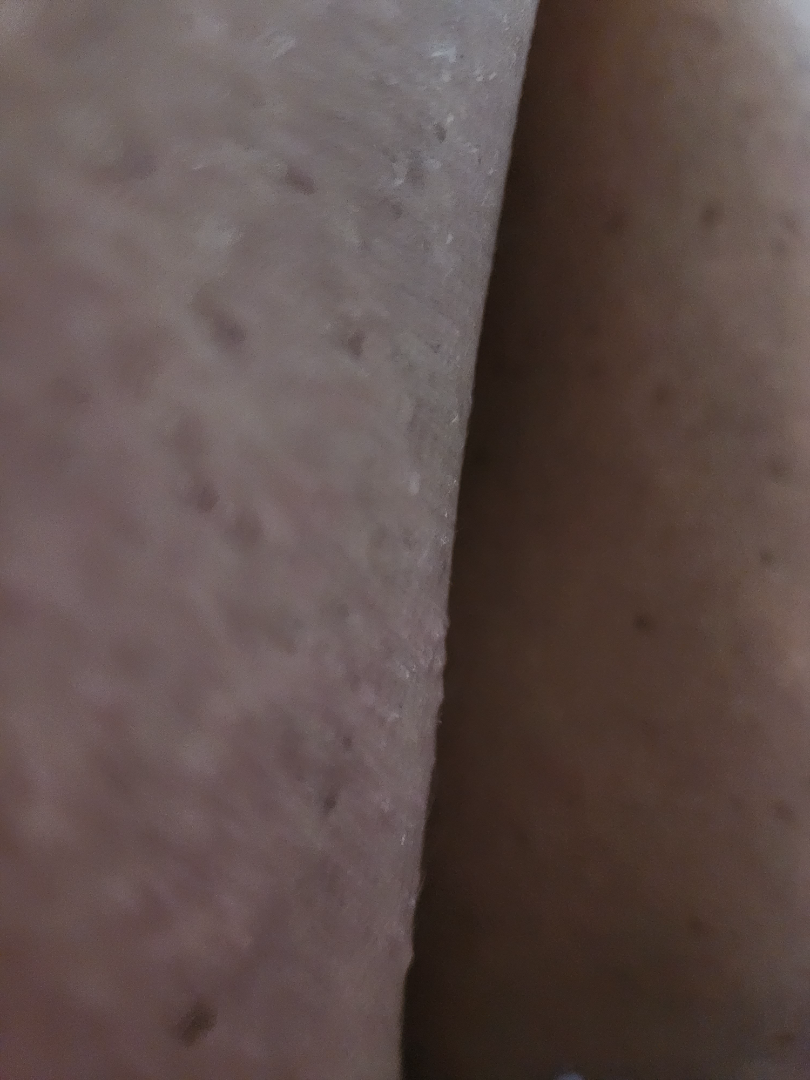Q: Anatomic location?
A: leg
Q: Who is the patient?
A: female, age 40–49
Q: Texture?
A: raised or bumpy
Q: What is the framing?
A: at an angle
Q: What symptoms does the patient report?
A: pain and itching
Q: Patient's own categorization?
A: a rash
Q: What conditions are considered?
A: Folliculitis (primary); Keratosis pilaris (considered); Lichen spinulosus (considered)